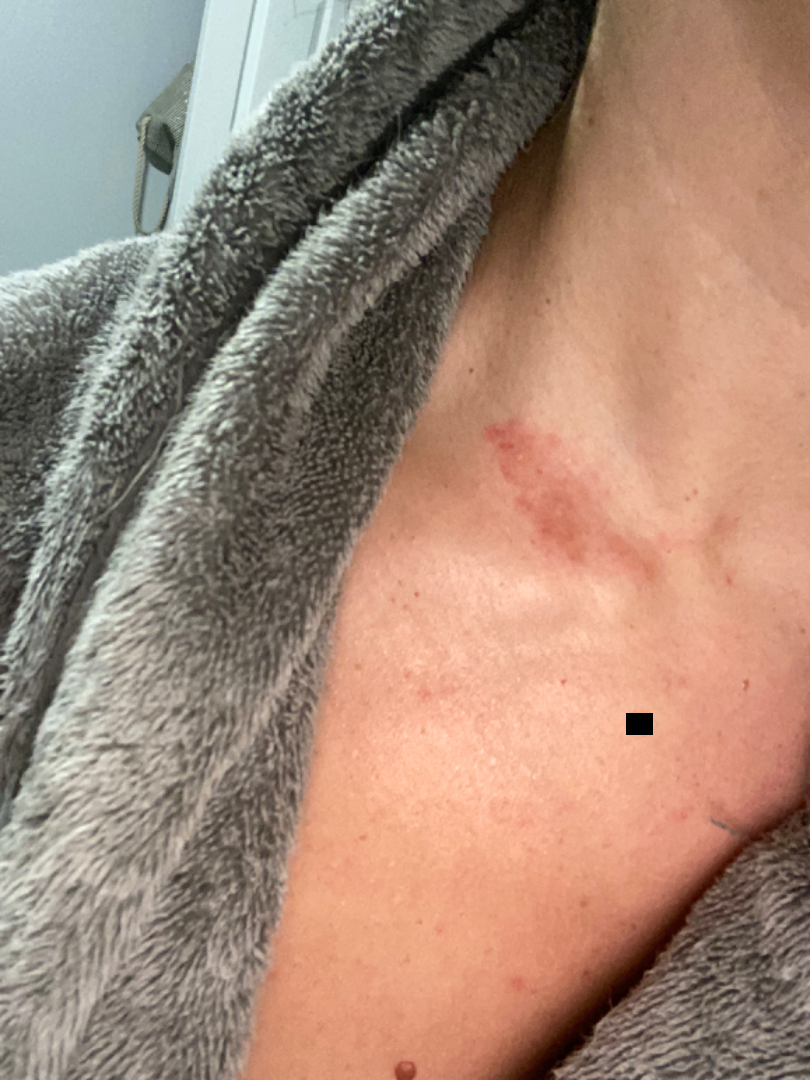assessment = not assessable; skin tone = Fitzpatrick IV; other reported symptoms = none reported; reported symptoms = bothersome appearance, enlargement and itching; patient's own categorization = a rash; duration = less than one week; described texture = raised or bumpy; site = head or neck; shot type = at an angle.